Reported lesion symptoms include bothersome appearance; close-up view; the patient described the issue as a pigmentary problem; the contributor notes the condition has been present for about one day; the contributor notes the lesion is flat.
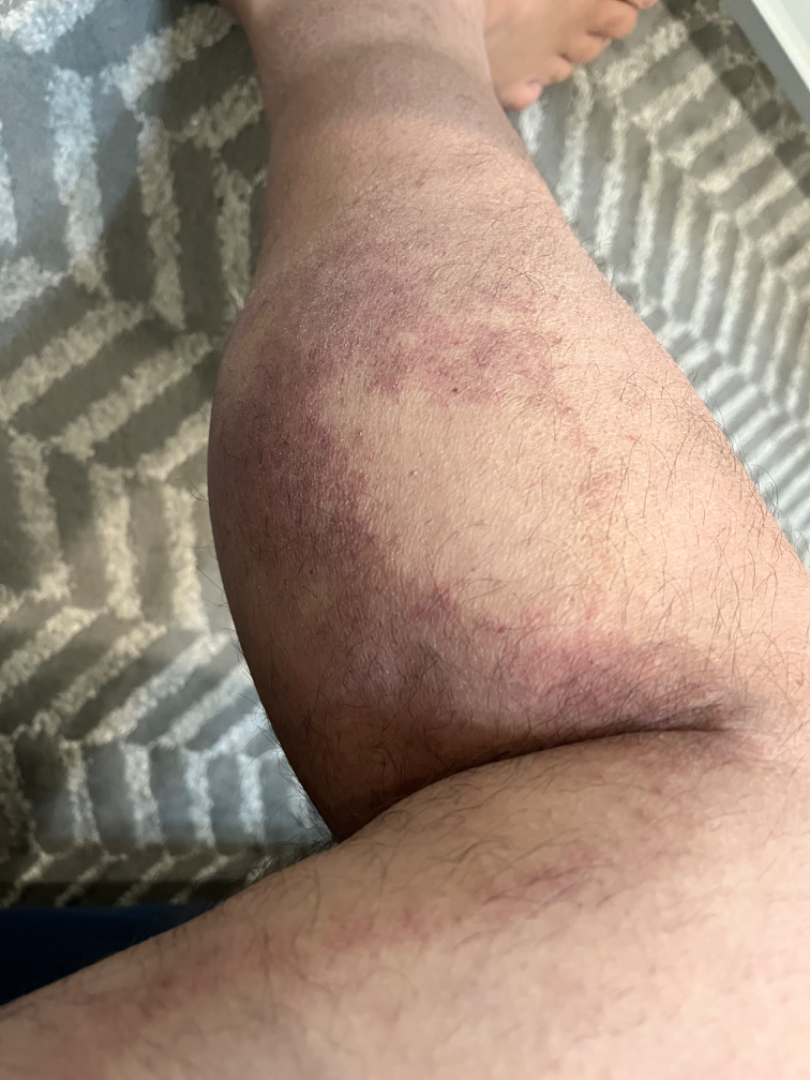A single dermatologist reviewed the case: the differential is split between Pigmented purpuric eruption, ecchymoses and Lichen planus/lichenoid eruption.